This image was taken at an angle, the arm is involved:
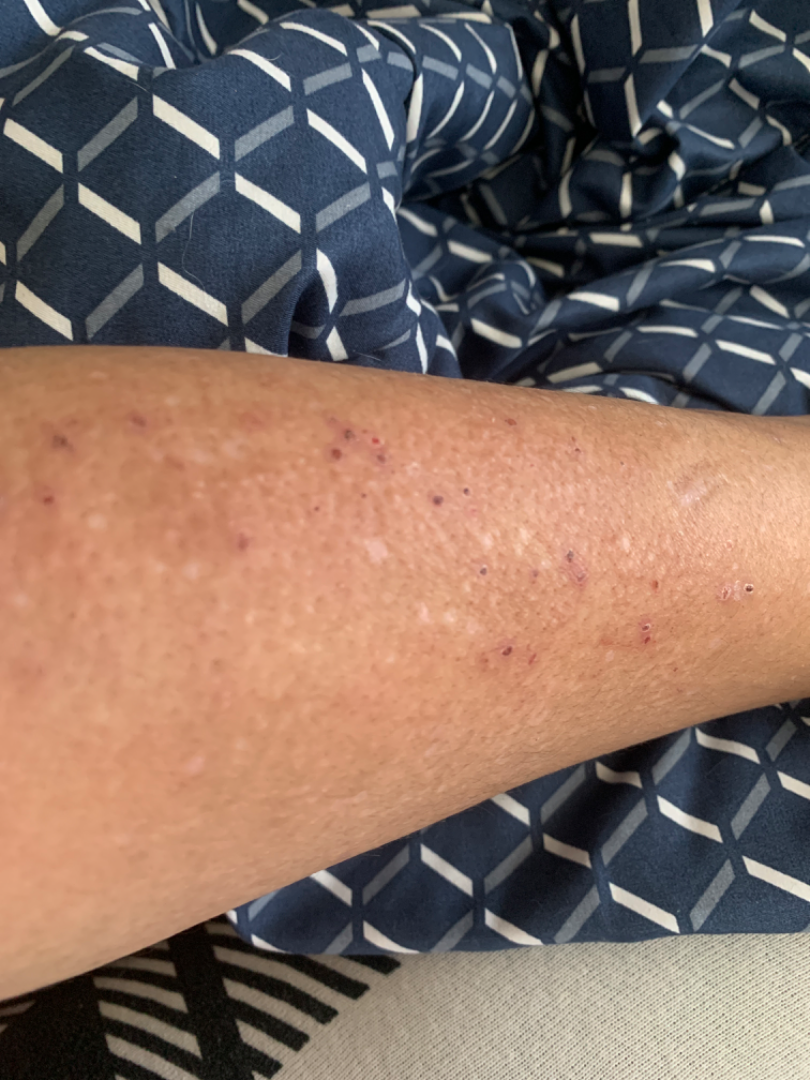Findings:
No differential diagnosis could be assigned on photographic review.